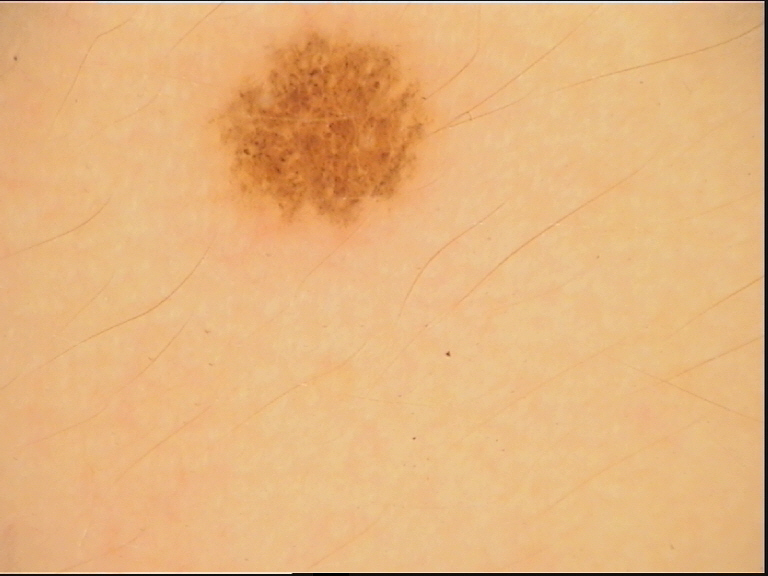Impression: Labeled as a dysplastic junctional nevus.